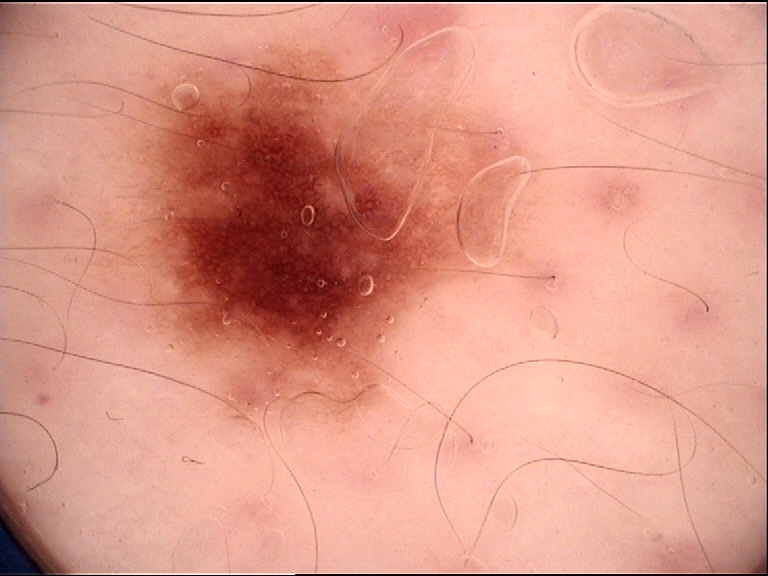Labeled as a benign lesion — a dysplastic junctional nevus.